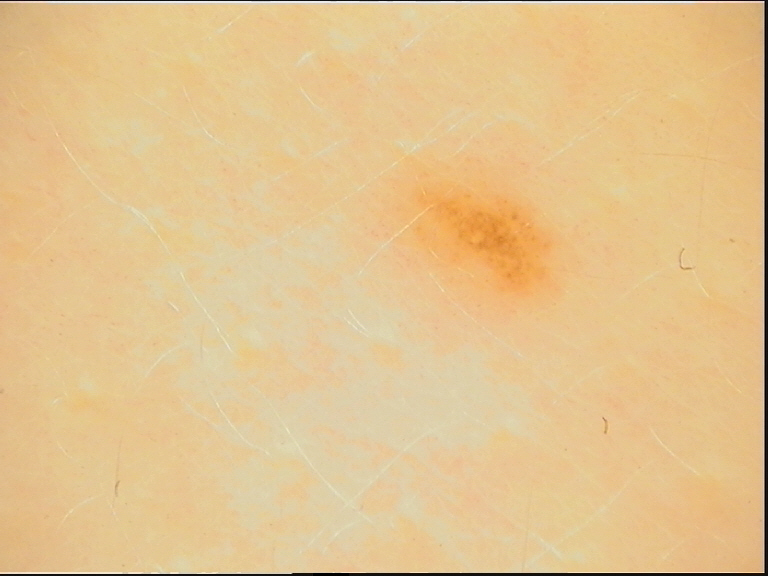Impression: Consistent with a junctional nevus.